The patient says their skin tans without first burning; the patient reports a personal history of cancer and a personal history of skin cancer; a female patient 60 years of age; the patient describes having few moles overall:
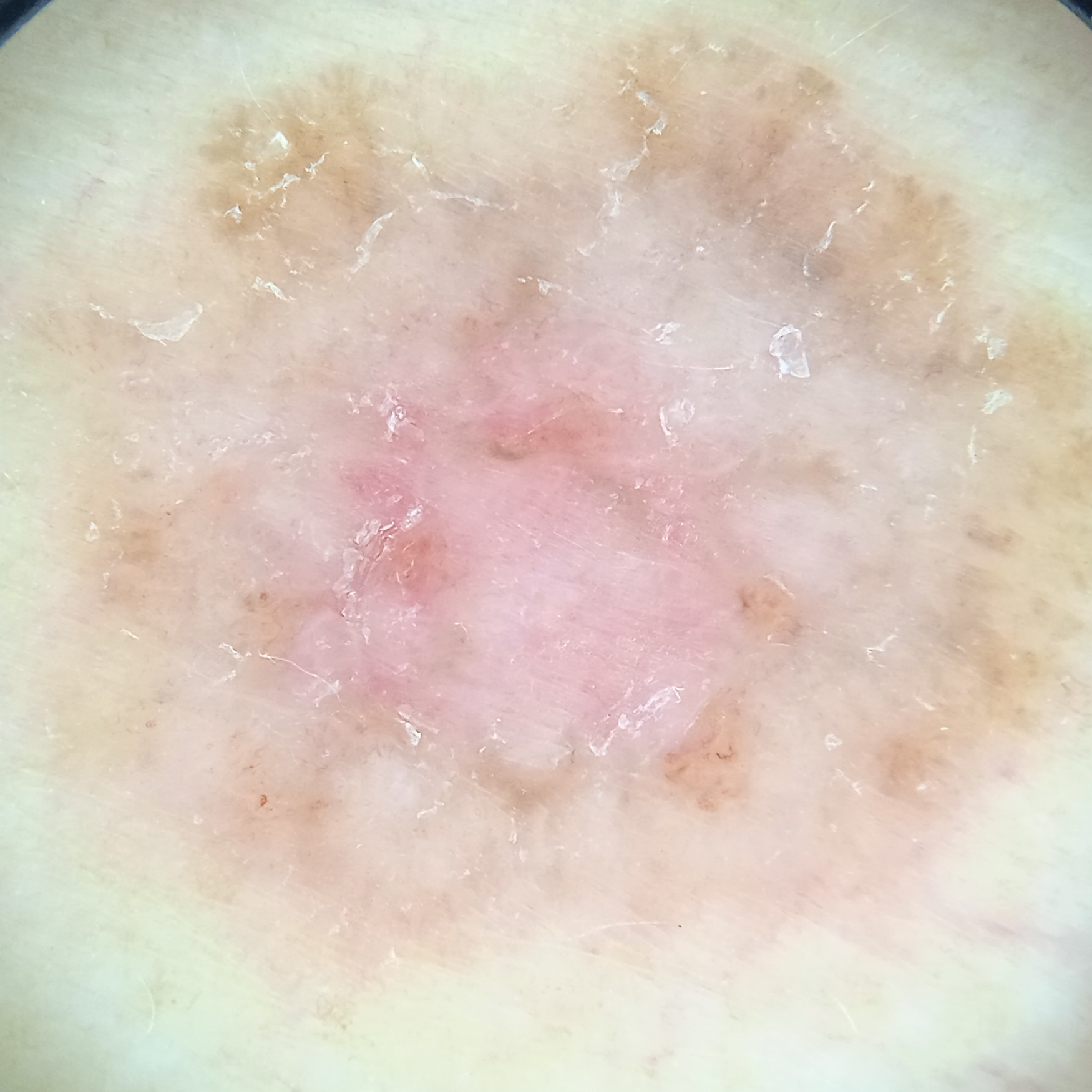site — the torso
diameter — 13.2 mm
assessment — basal cell carcinoma (dermatologist consensus)